The photograph was taken at an angle; located on the arm: 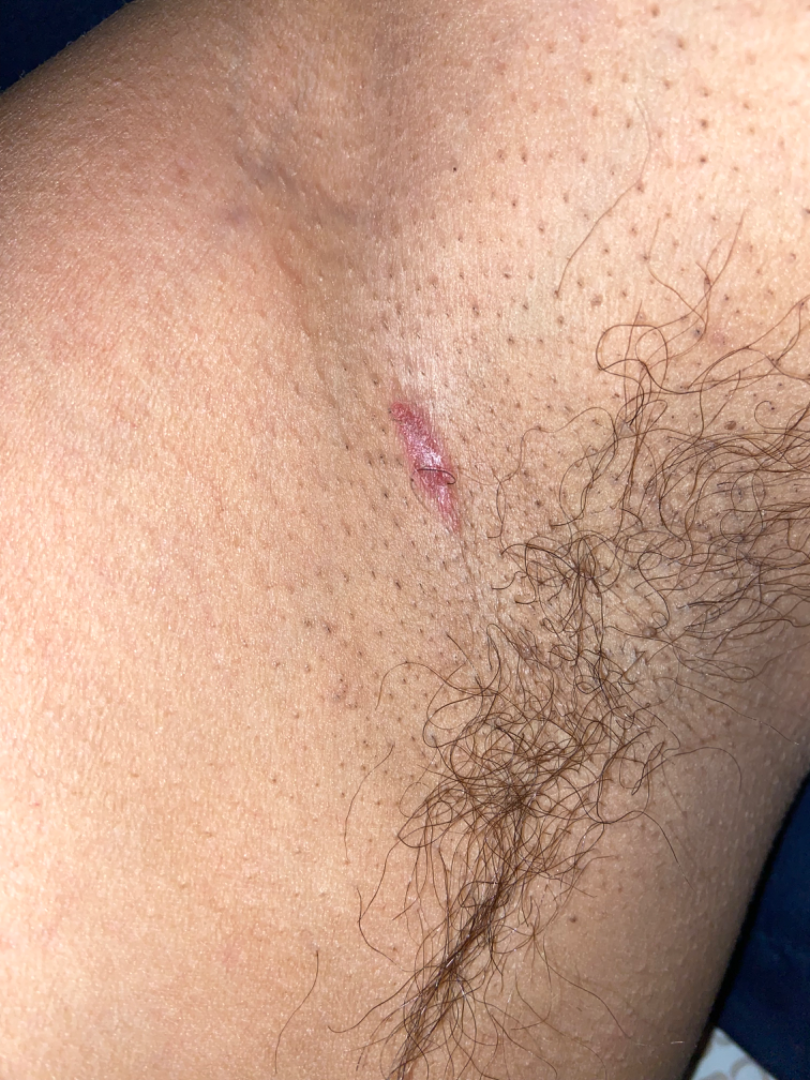| key | value |
|---|---|
| assessment | not assessable |
| duration | one to four weeks |
| lesion texture | flat and rough or flaky |
| patient describes the issue as | a rash |
| other reported symptoms | none reported |
| reported symptoms | bothersome appearance, pain and burning |